Located on the arm; the photo was captured at a distance; female patient, age 18–29 — 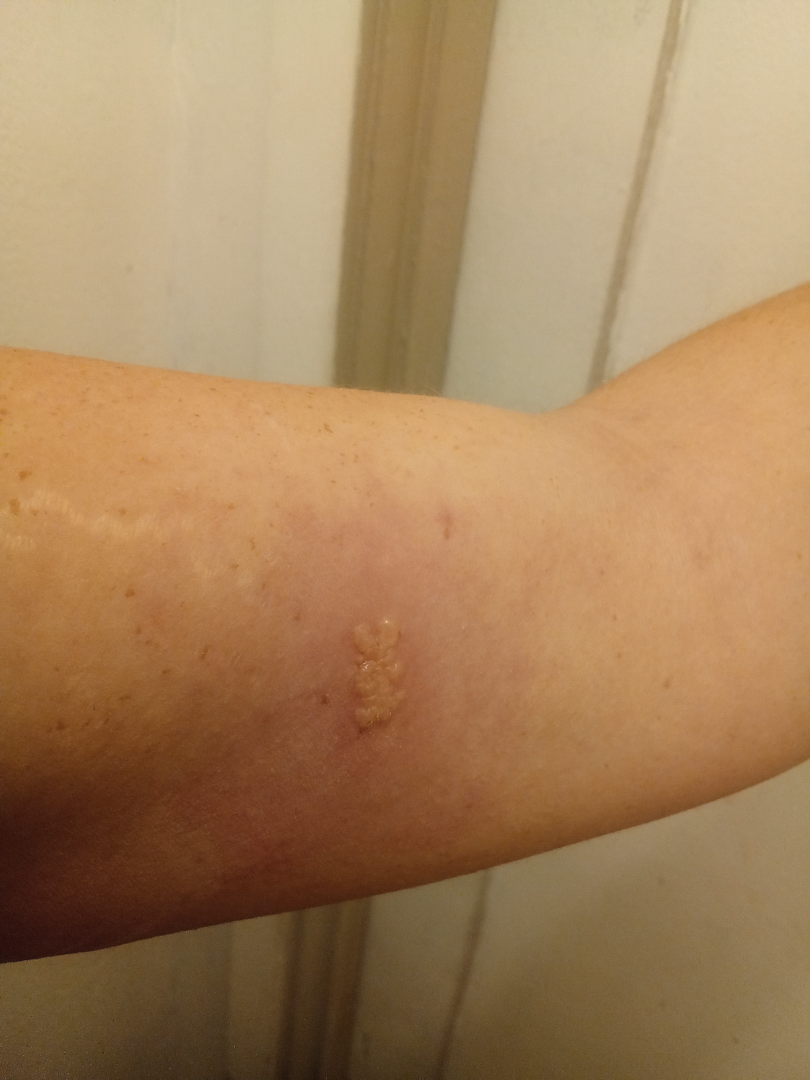Symptoms reported: itching and burning. Present for more than one year. On remote dermatologist review, the impression was split between Herpes Zoster and Herpes Simplex; less probable is Allergic Contact Dermatitis.